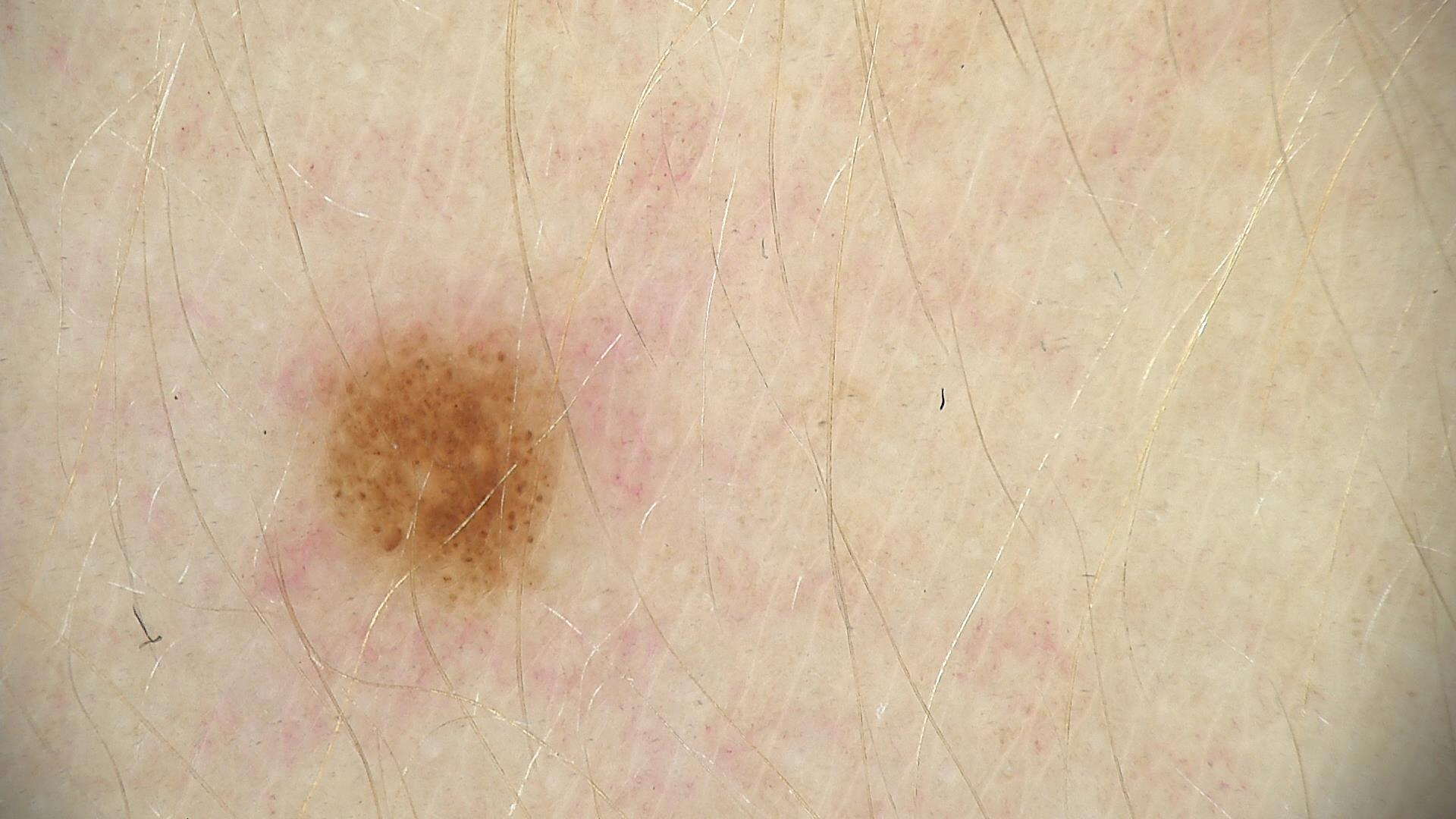Q: What is this lesion?
A: dysplastic junctional nevus (expert consensus)